Dermoscopy of a skin lesion; the patient says their skin reddens with sun exposure; collected as part of a research study, without a referral diagnosis.
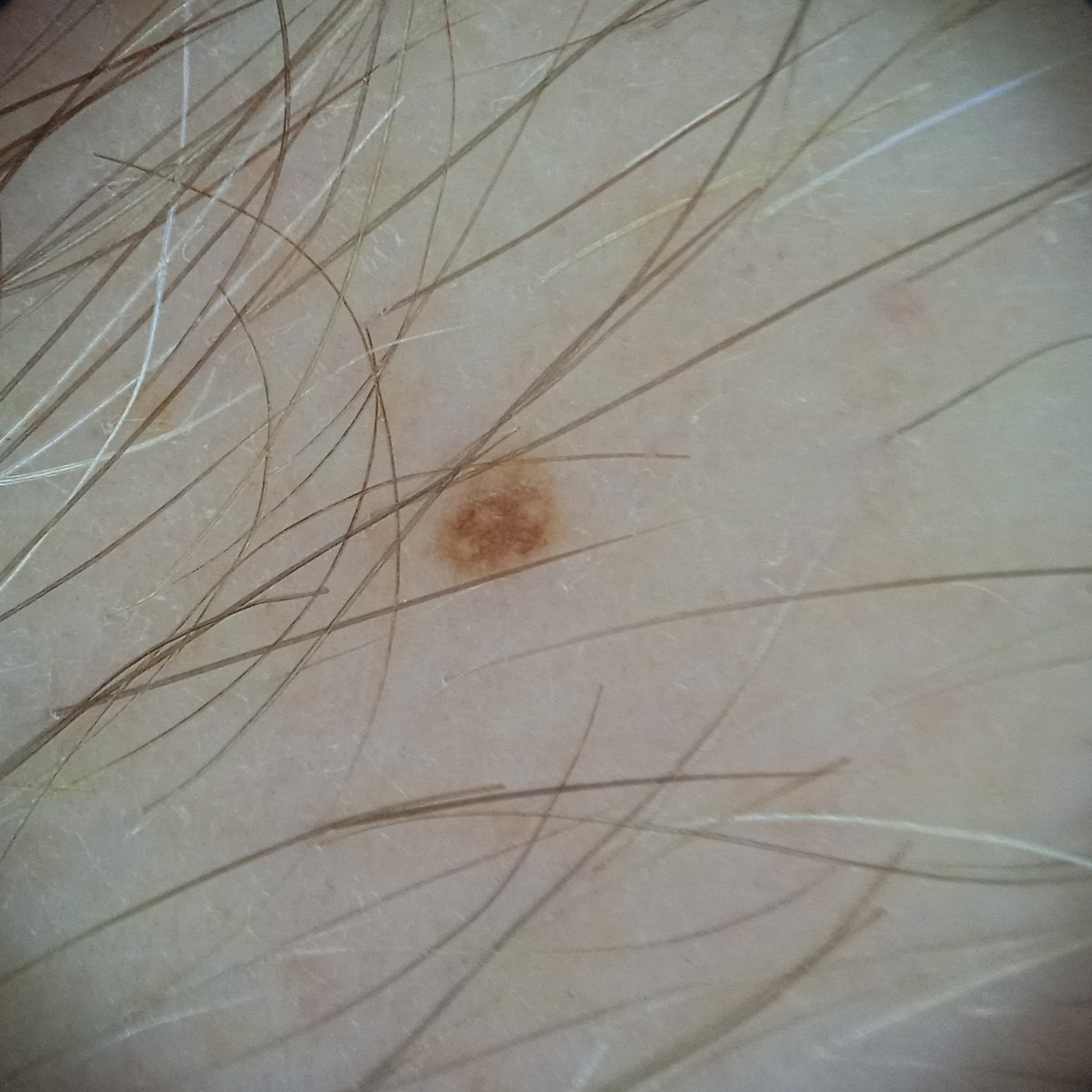The lesion is about 1.5 mm across. Reviewed by four dermatologists, the consensus diagnosis was a melanocytic nevus.